A dermatoscopic image of a skin lesion: 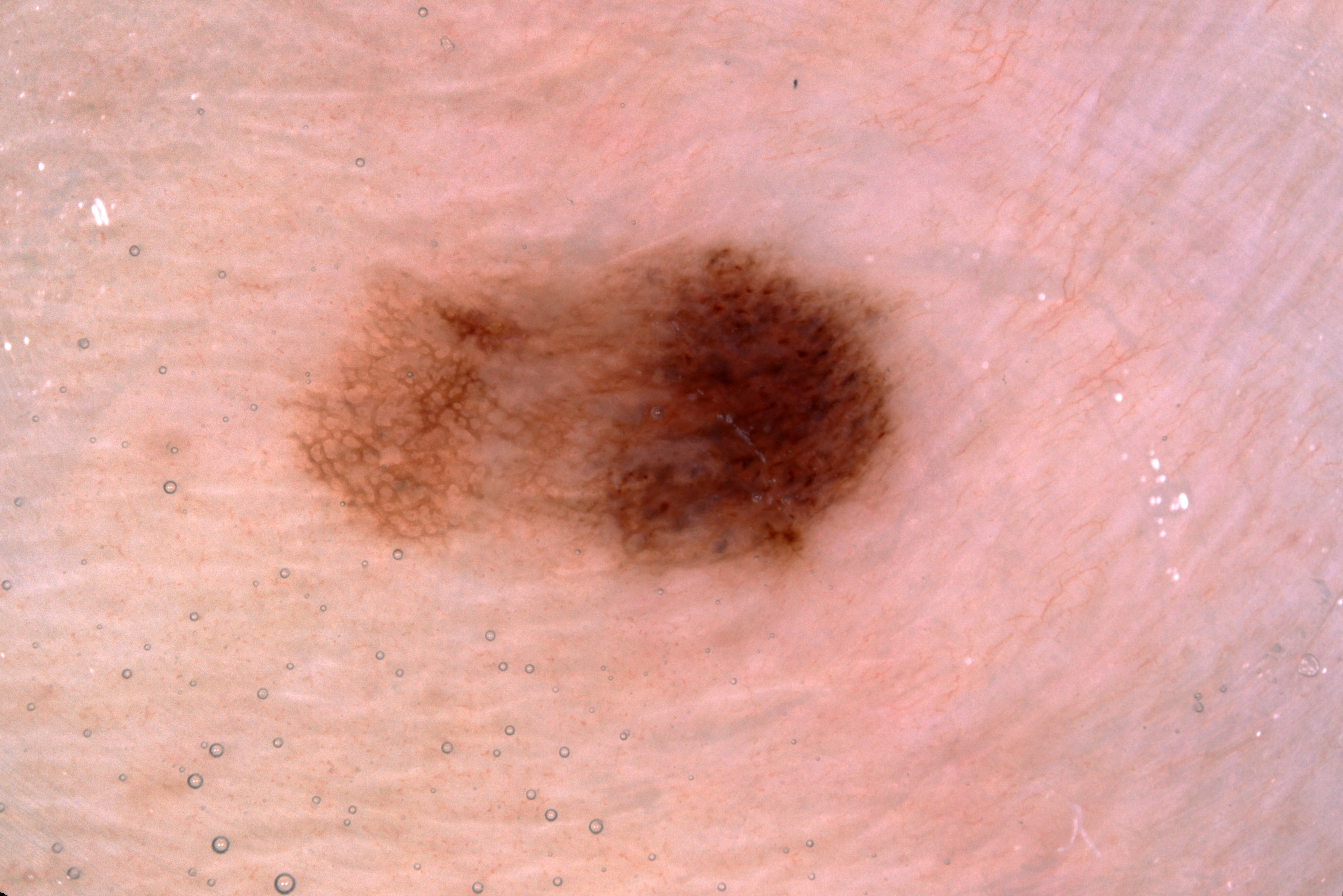Q: What is the lesion's bounding box?
A: (276, 231, 922, 606)
Q: What is this lesion?
A: a melanocytic nevus